The head or neck, arm, front of the torso, back of the torso and leg are involved · the photo was captured at a distance.
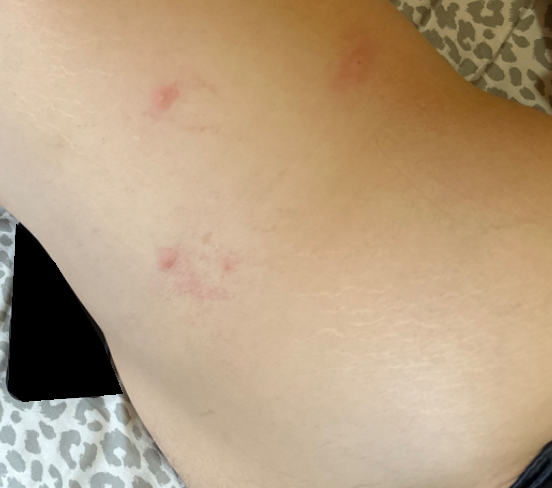Case summary:
* patient describes the issue as · a rash
* onset · about one day
* reported symptoms · pain, burning and itching
* described texture · fluid-filled
* dermatologist impression · most likely Scar Condition; an alternative is Folliculitis; also on the differential is Acne